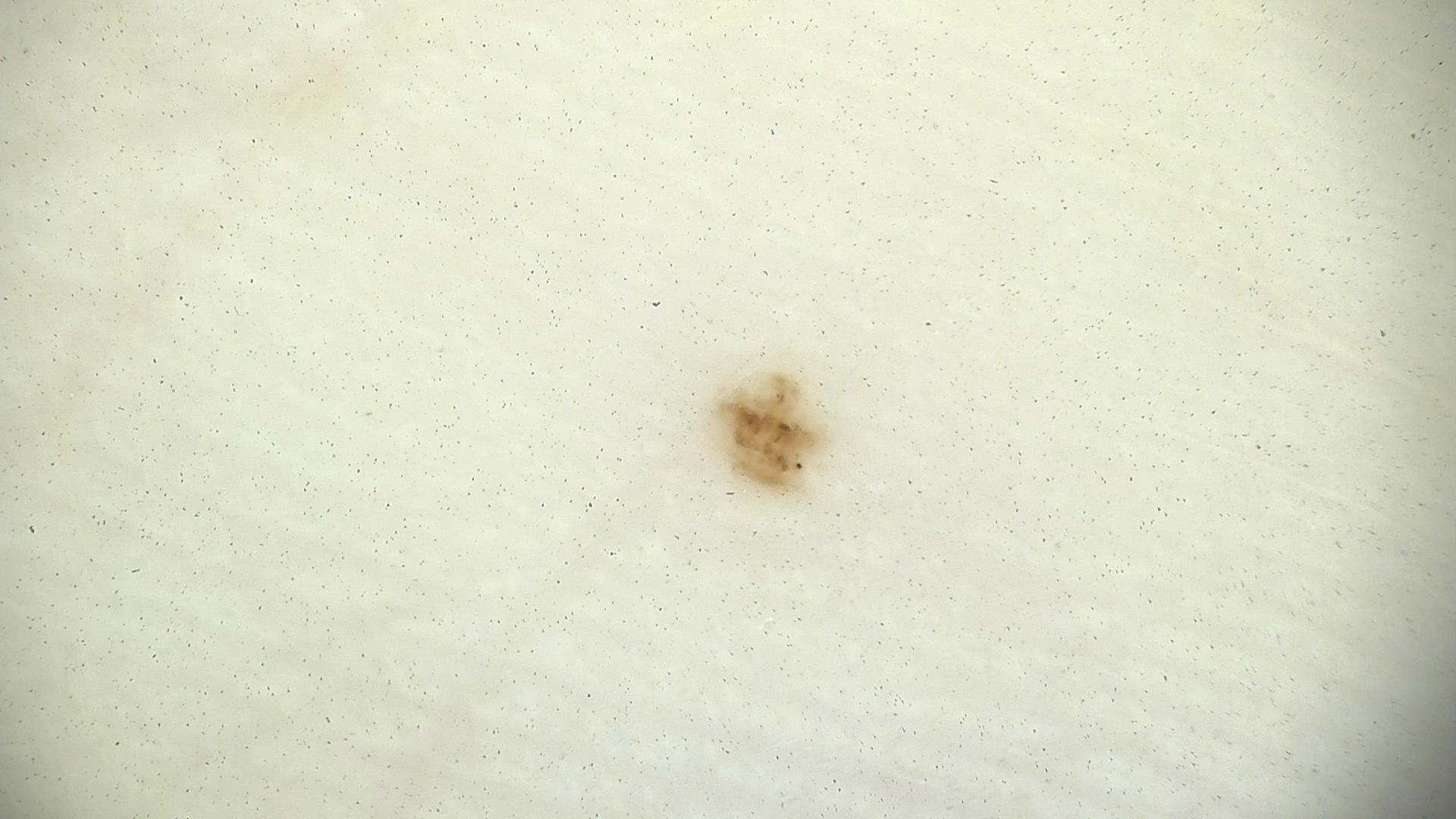diagnosis:
  name: acral dysplastic junctional nevus
  code: ajd
  malignancy: benign
  super_class: melanocytic
  confirmation: expert consensus